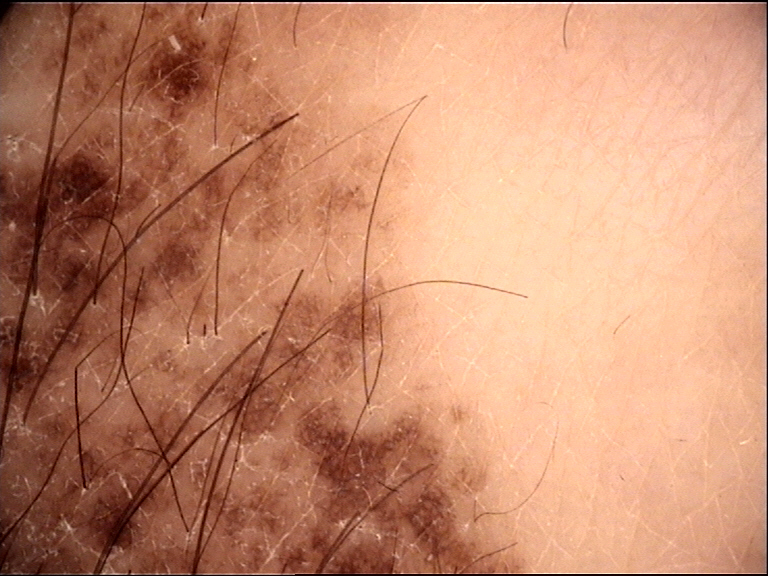Labeled as a congenital compound nevus.